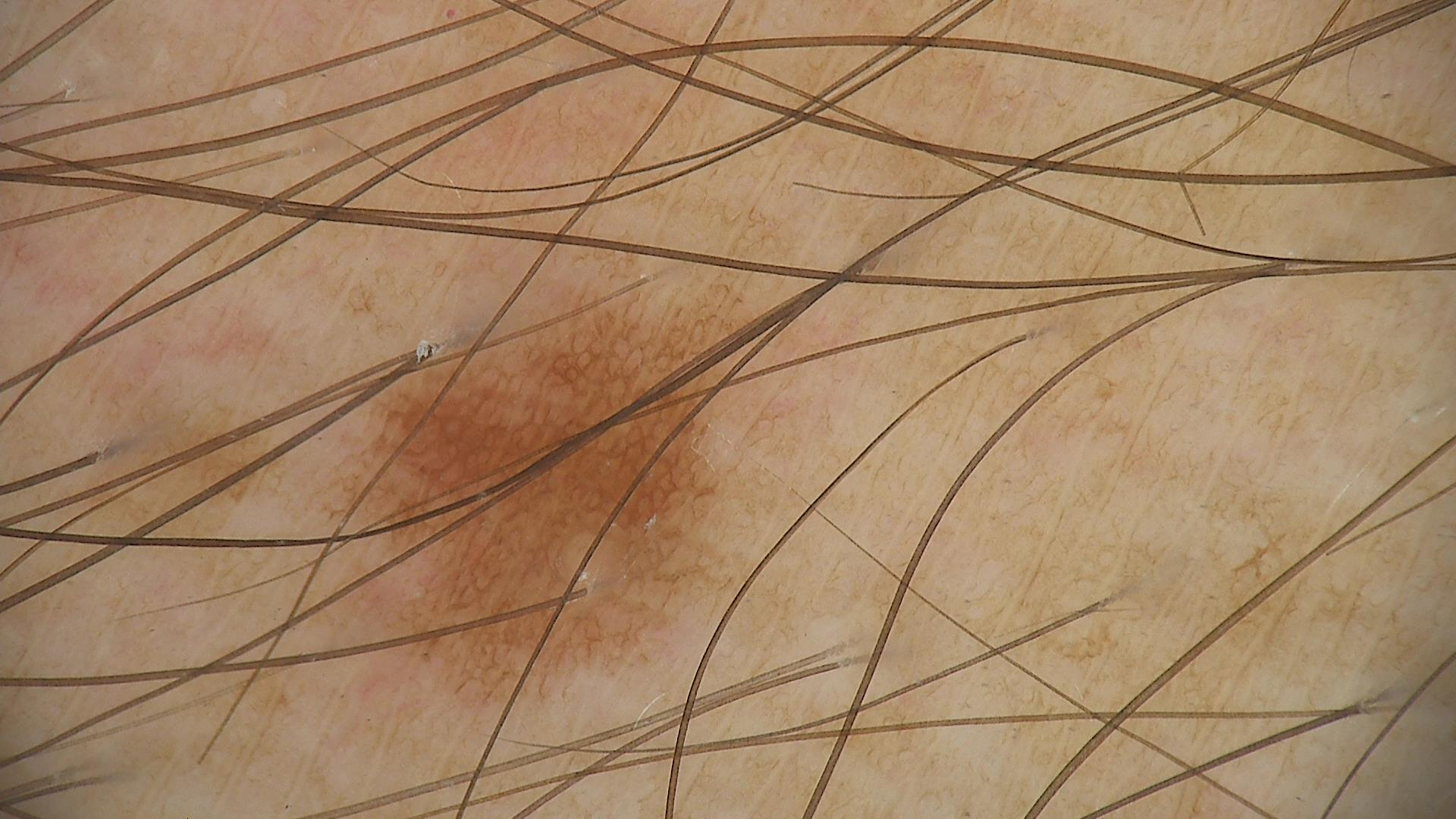diagnosis = junctional nevus (expert consensus).